A clinical photo of a skin lesion taken with a smartphone; the chart records alcohol use, prior skin cancer (patient or family), tobacco use, pesticide exposure, and prior malignancy (patient or family); a male patient in their 70s.
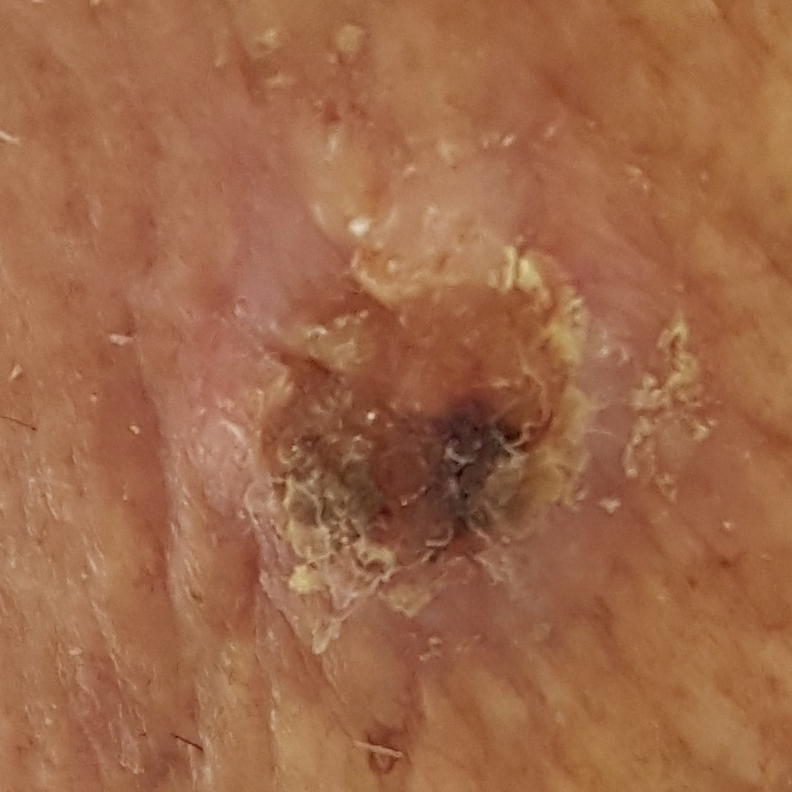site: the neck; size: approx. 10 × 6 mm; diagnostic label: basal cell carcinoma (biopsy-proven).